The lesion is described as raised or bumpy and rough or flaky · the lesion involves the arm · the lesion is associated with bothersome appearance, itching, pain, darkening and burning · the subject is female · reported duration is less than one week · the patient considered this a rash · an image taken at a distance: 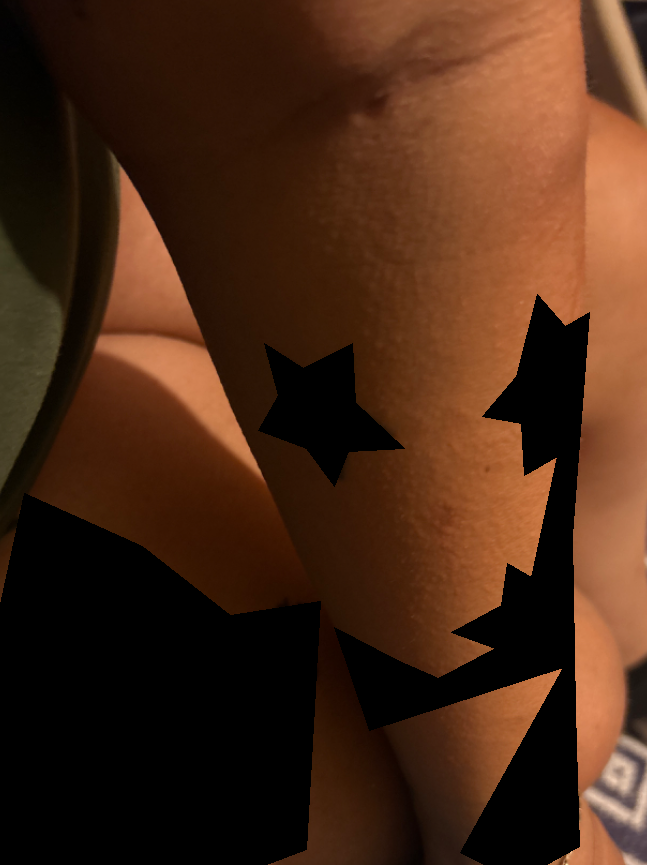Q: What is the differential diagnosis?
A: three dermatologists each reviewed the case: Urticaria, Eczema and Allergic Contact Dermatitis were considered with similar weight